A dermatoscopic image of a skin lesion:
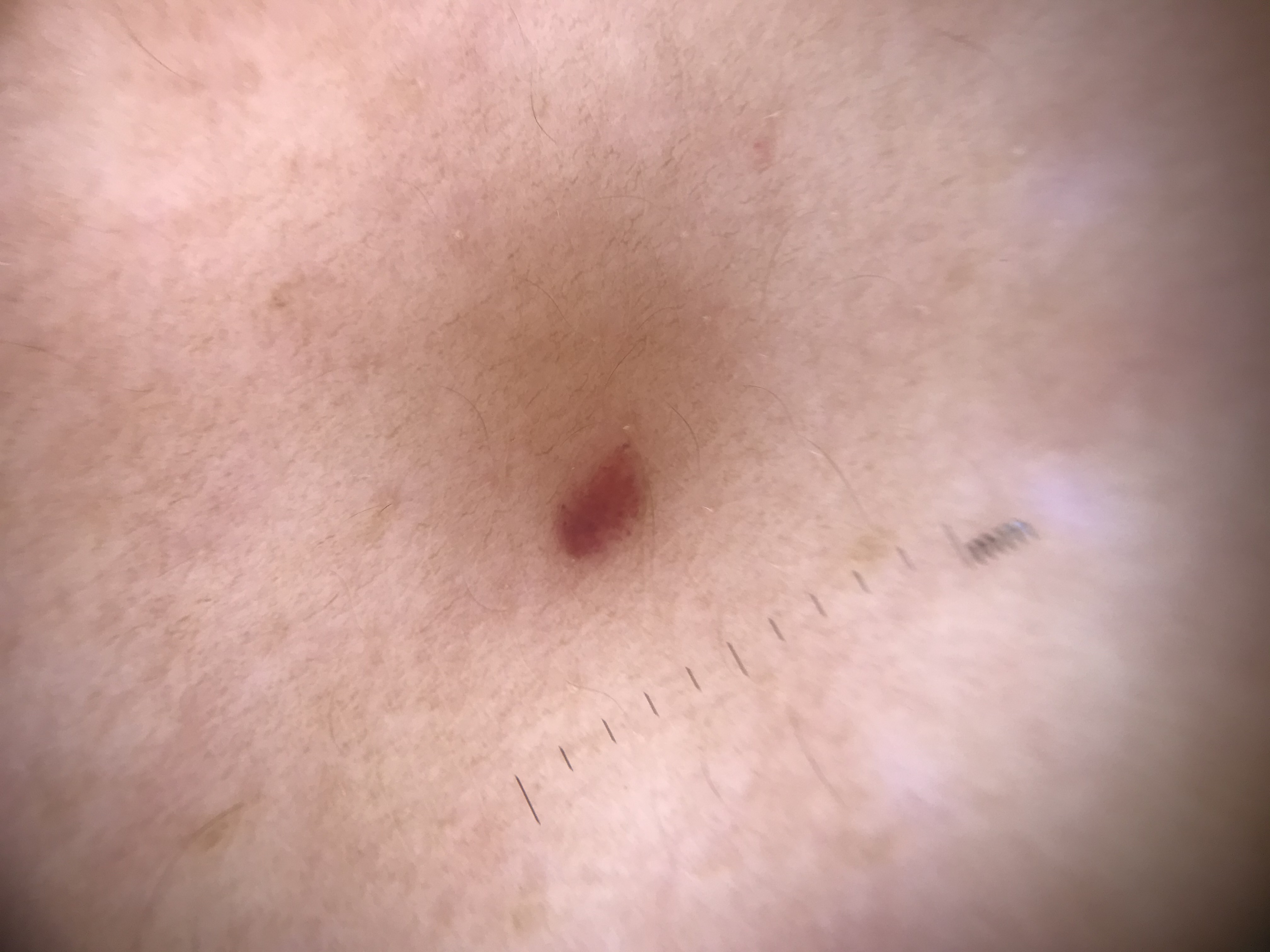The architecture is that of a vascular lesion. Classified as a hemangioma.